The patient was assessed as Fitzpatrick skin type II; a dermoscopic image of a skin lesion; a male subject aged around 65.
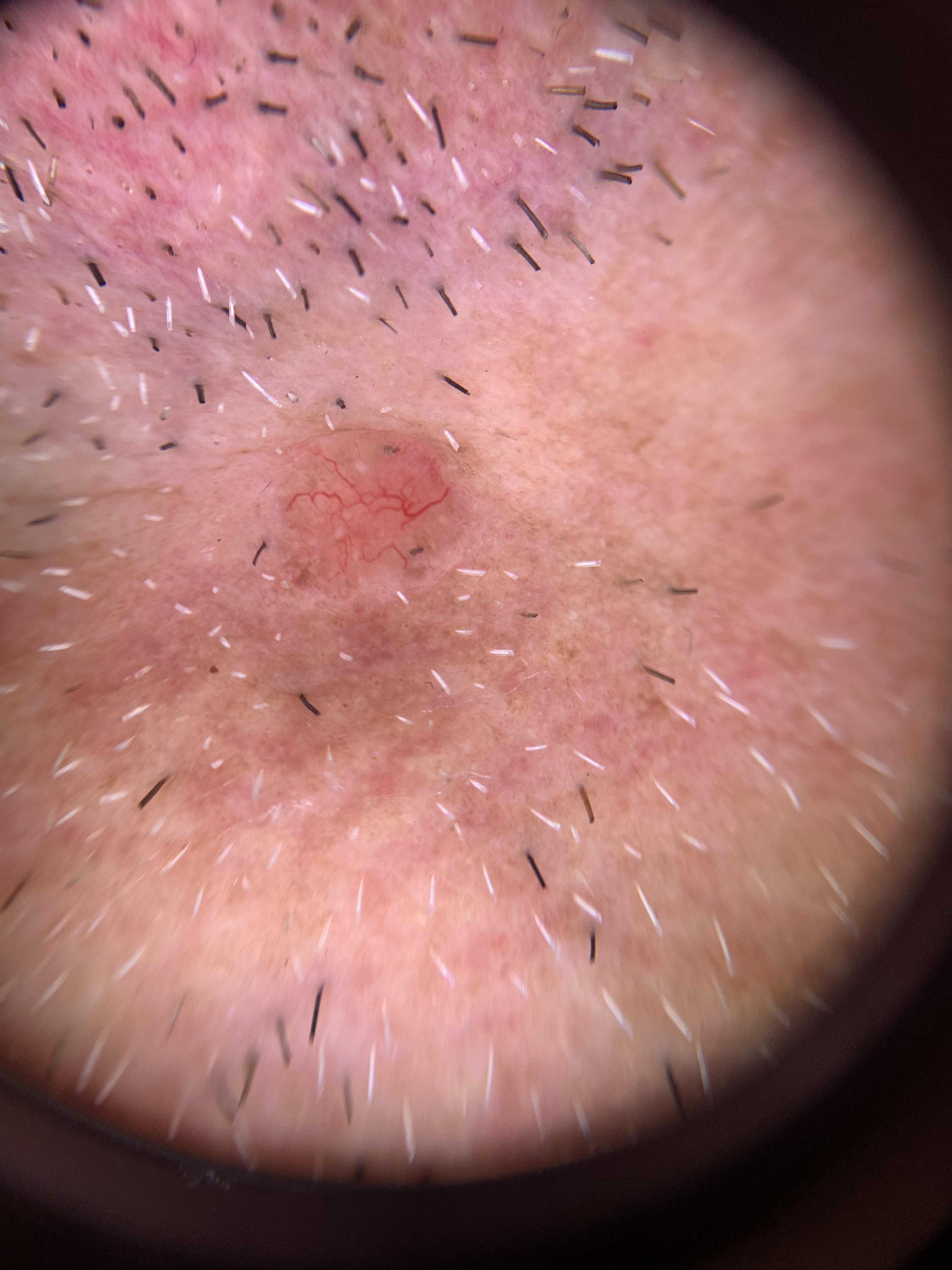Conclusion: Histopathological examination showed a malignancy — a basal cell carcinoma.